The patient says their skin tans without first burning. Acquired for a research image collection, with no referral diagnosis. A macroscopic clinical photograph of a skin lesion. A female patient 67 years old. The patient describes having few moles overall.
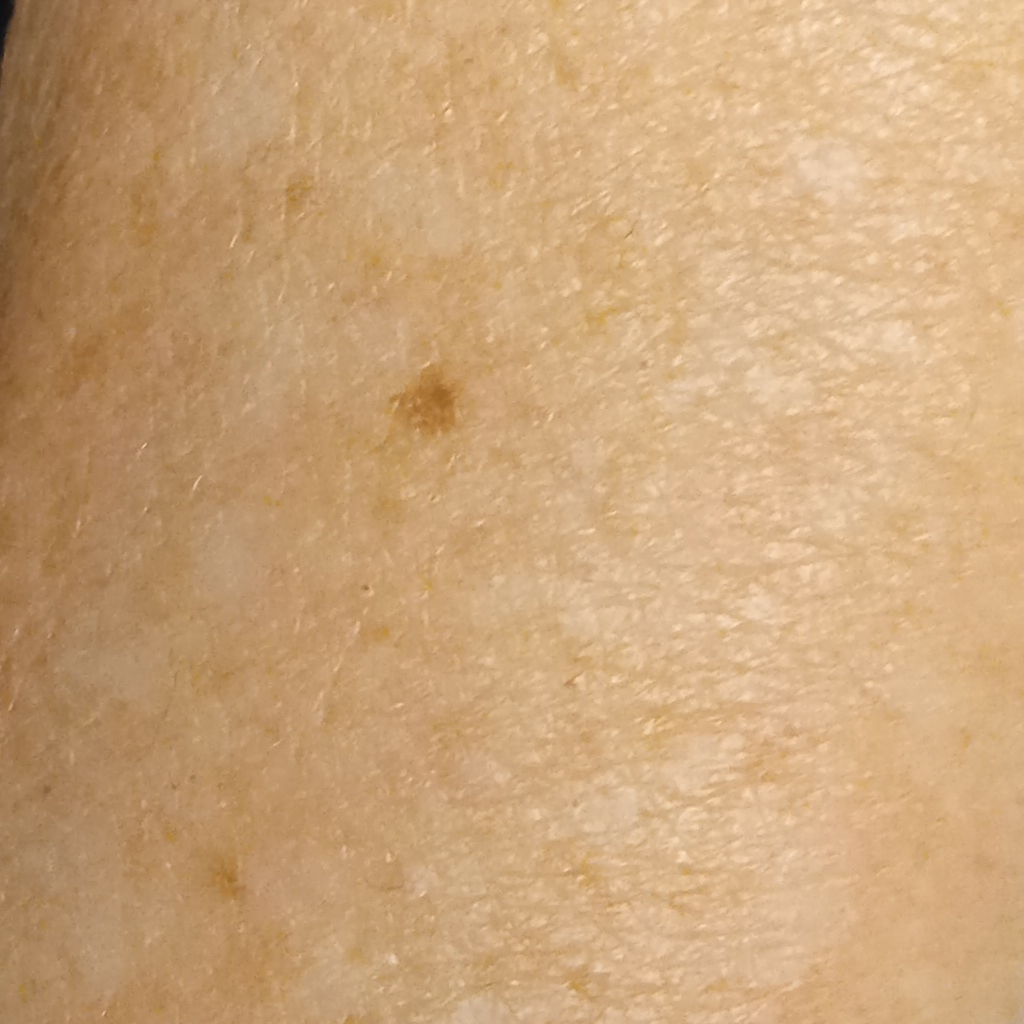The lesion involves an arm. The lesion measures approximately 2.1 mm. The consensus diagnosis for this lesion was a melanocytic nevus.